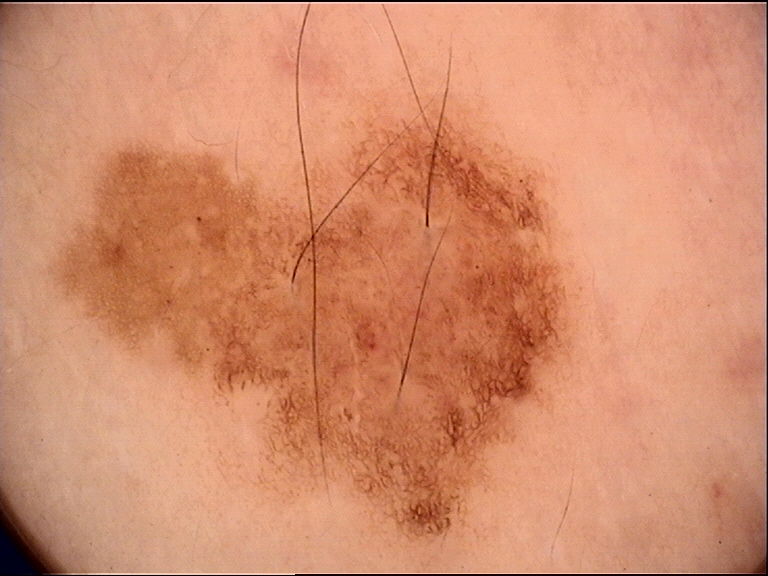class — dysplastic junctional nevus (expert consensus)